A dermoscopy image of a single skin lesion · a male patient about 75 years old:
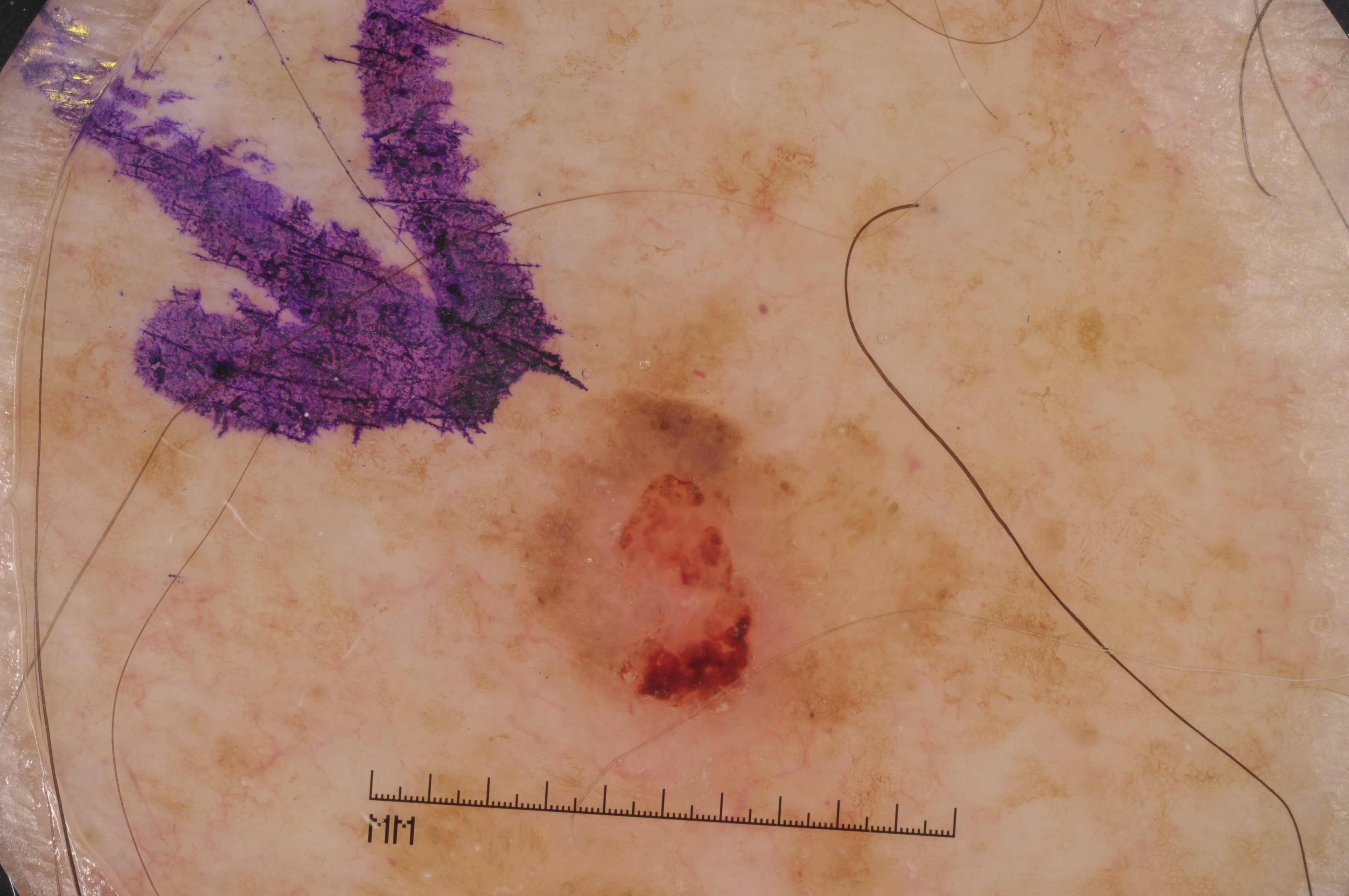A moderately sized lesion.
As (left, top, right, bottom), the visible lesion spans <bbox>487, 390, 970, 731</bbox>.
On dermoscopy, the lesion shows milia-like cysts and pigment network, with no streaks or negative network.
The lesion was assessed as a seborrheic keratosis, a benign lesion.